The lesion involves the leg, palm and arm; this is a close-up image; female subject, age 50–59.
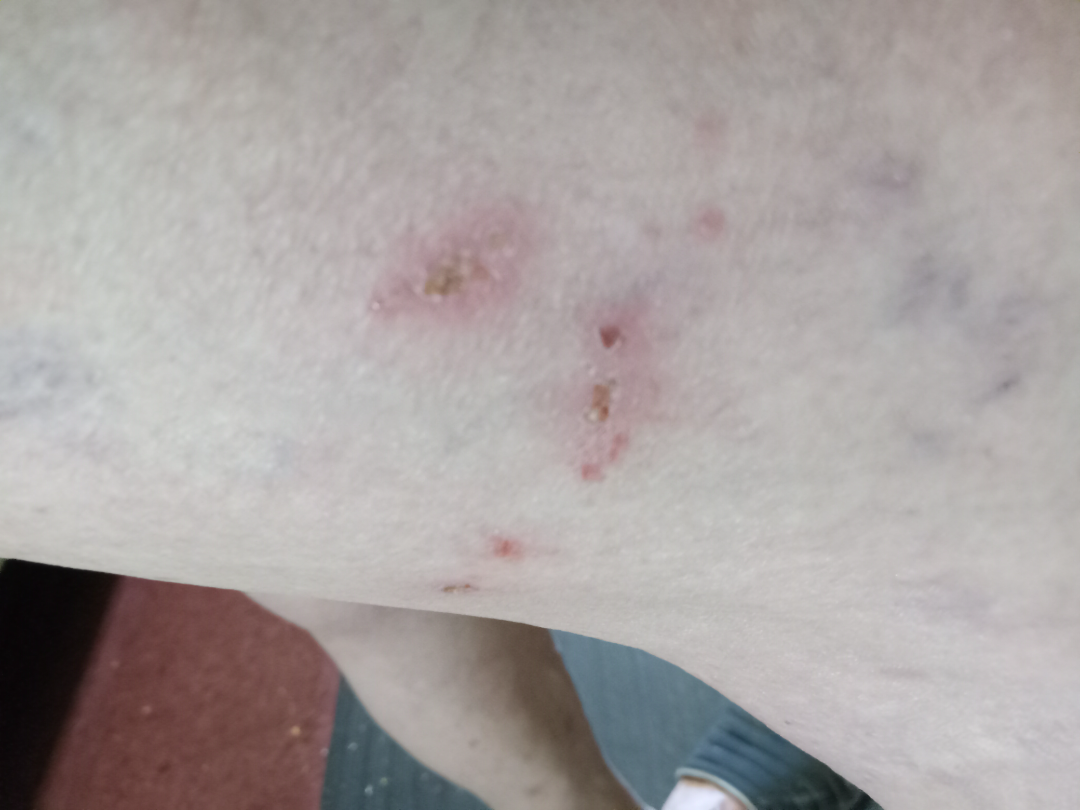Assessment:
Inflicted skin lesions and Eczema were each considered, in no particular order; a more distant consideration is Impetigo; less likely is Localised skin infection.